The patient describes having a moderate number of moles · by self-report, no immunosuppression · a dermoscopic image of a skin lesion · imaged for a research study, with no referral diagnosis recorded · the patient says their skin reddens with sun exposure · a female patient age 59.
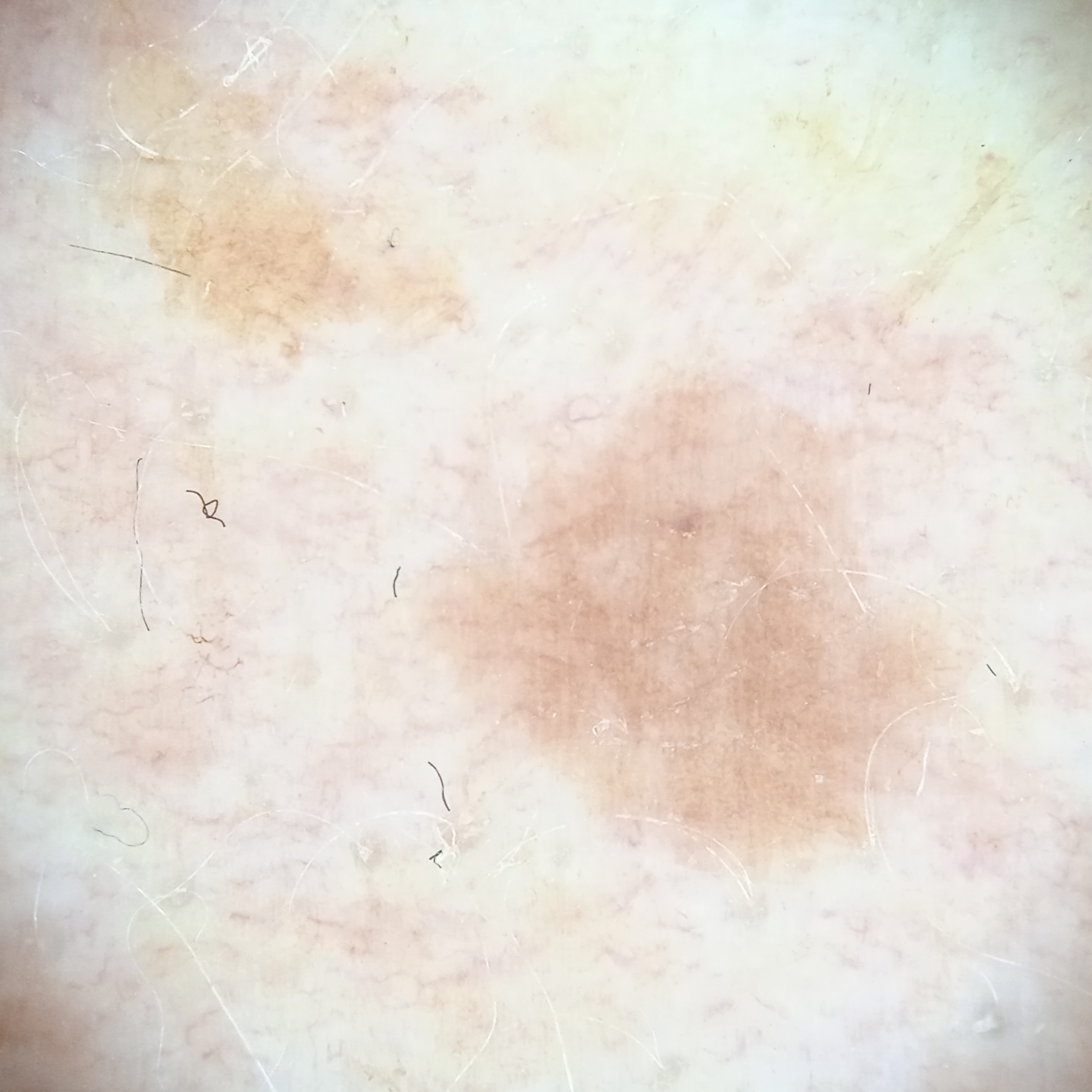site: an arm; diameter: 6.5 mm; diagnosis: melanocytic nevus (dermatologist consensus).